A dermoscopy image of a single skin lesion. A female patient, about 35 years old:
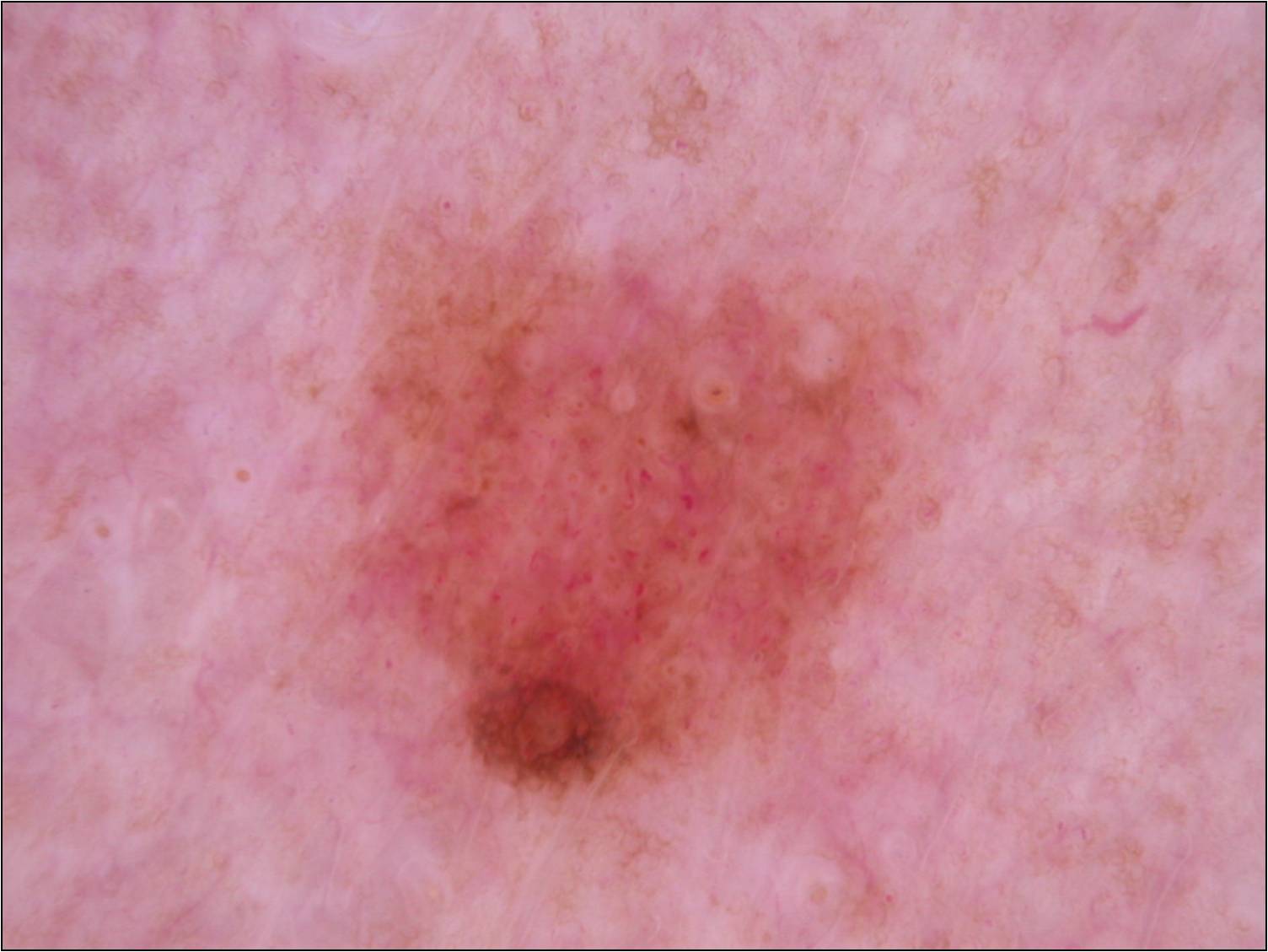Case summary:
– lesion bbox: <bbox>337, 214, 916, 812</bbox>
– dermoscopic features: pigment network and globules
– size: ~19% of the field
– diagnostic label: a melanocytic nevus